A dermoscopic photograph of a skin lesion: 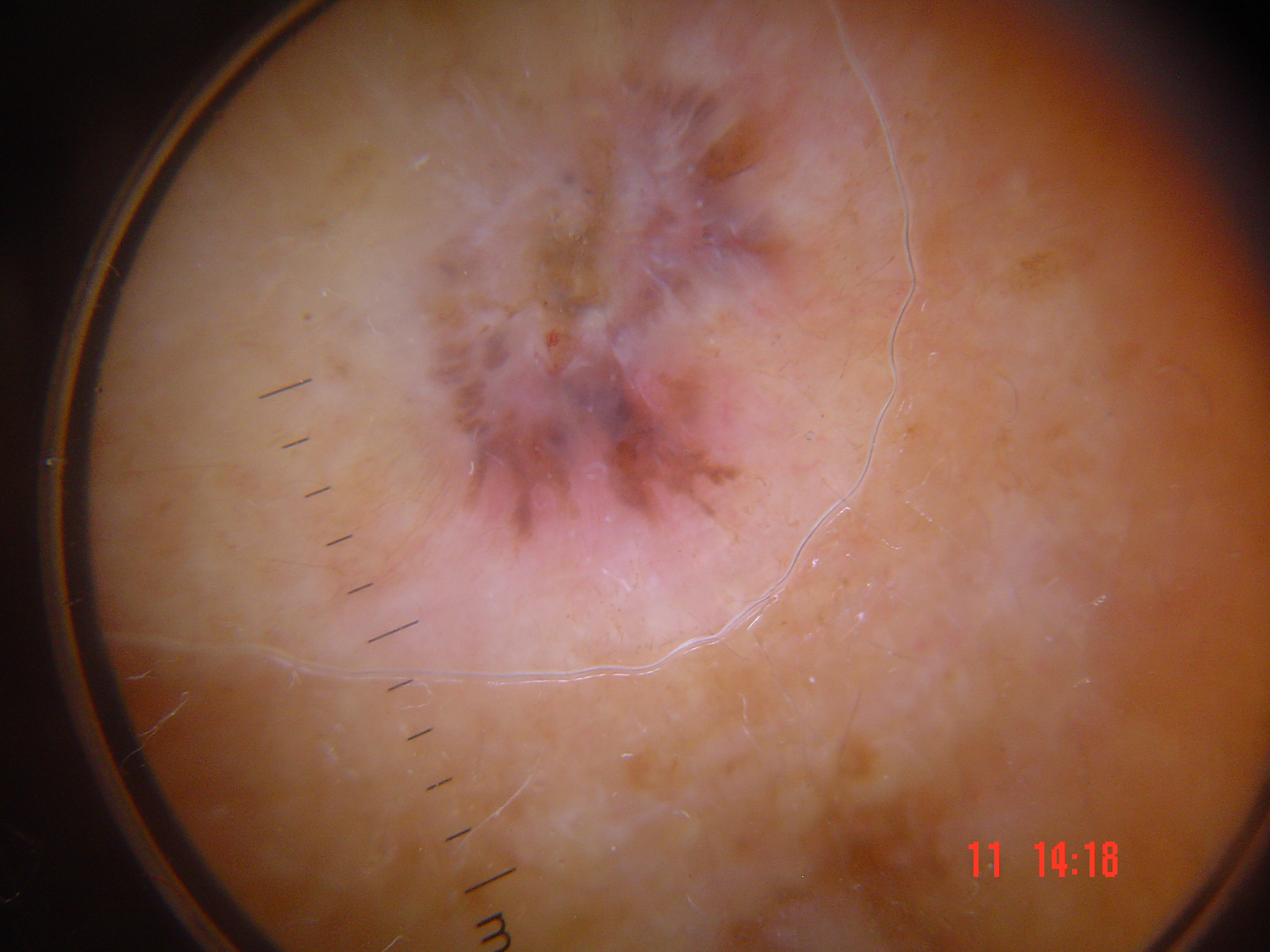diagnostic label=basal cell carcinoma (biopsy-proven).